A male patient approximately 30 years of age; a contact-polarized dermoscopy image of a skin lesion: 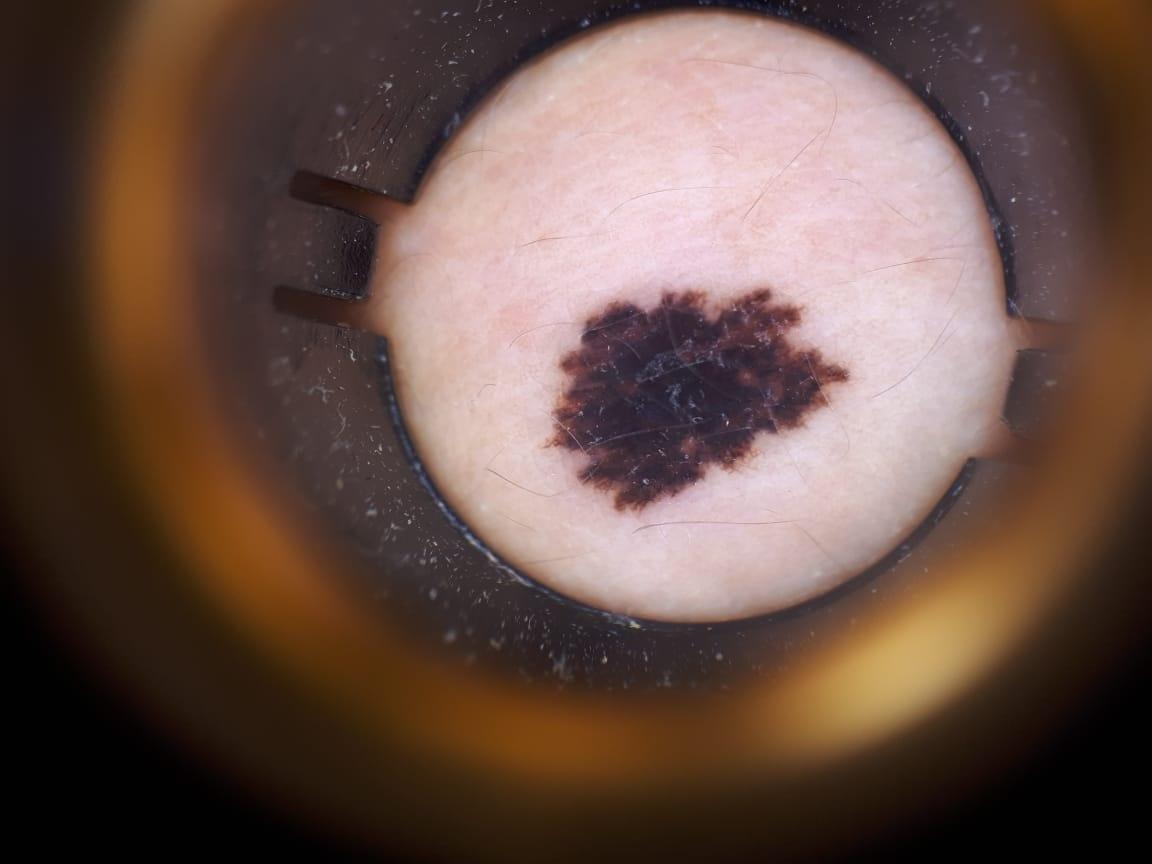body site: the trunk | pathology: Melanoma (biopsy-proven).